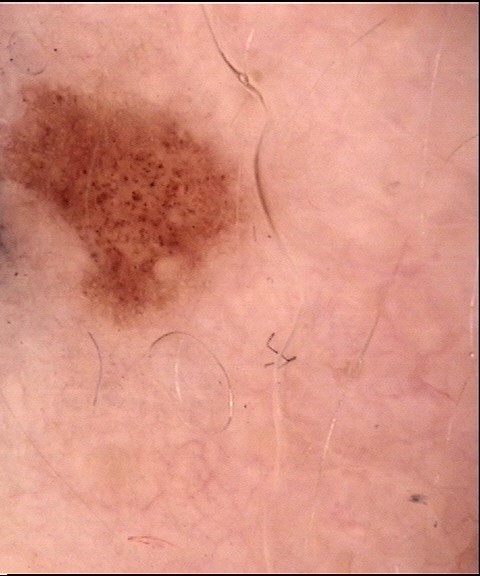Classified as a dysplastic junctional nevus.